A dermatoscopic image of a skin lesion: 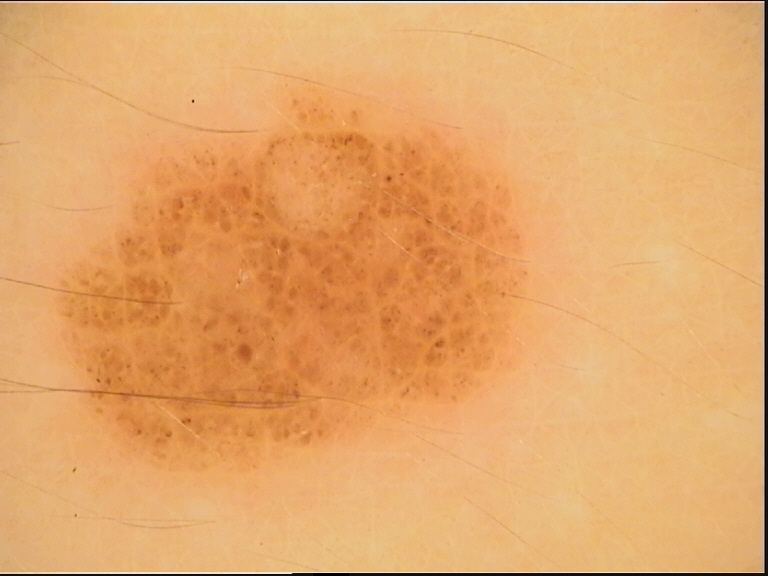This is a keratinocytic lesion. Diagnosed as a seborrheic keratosis.